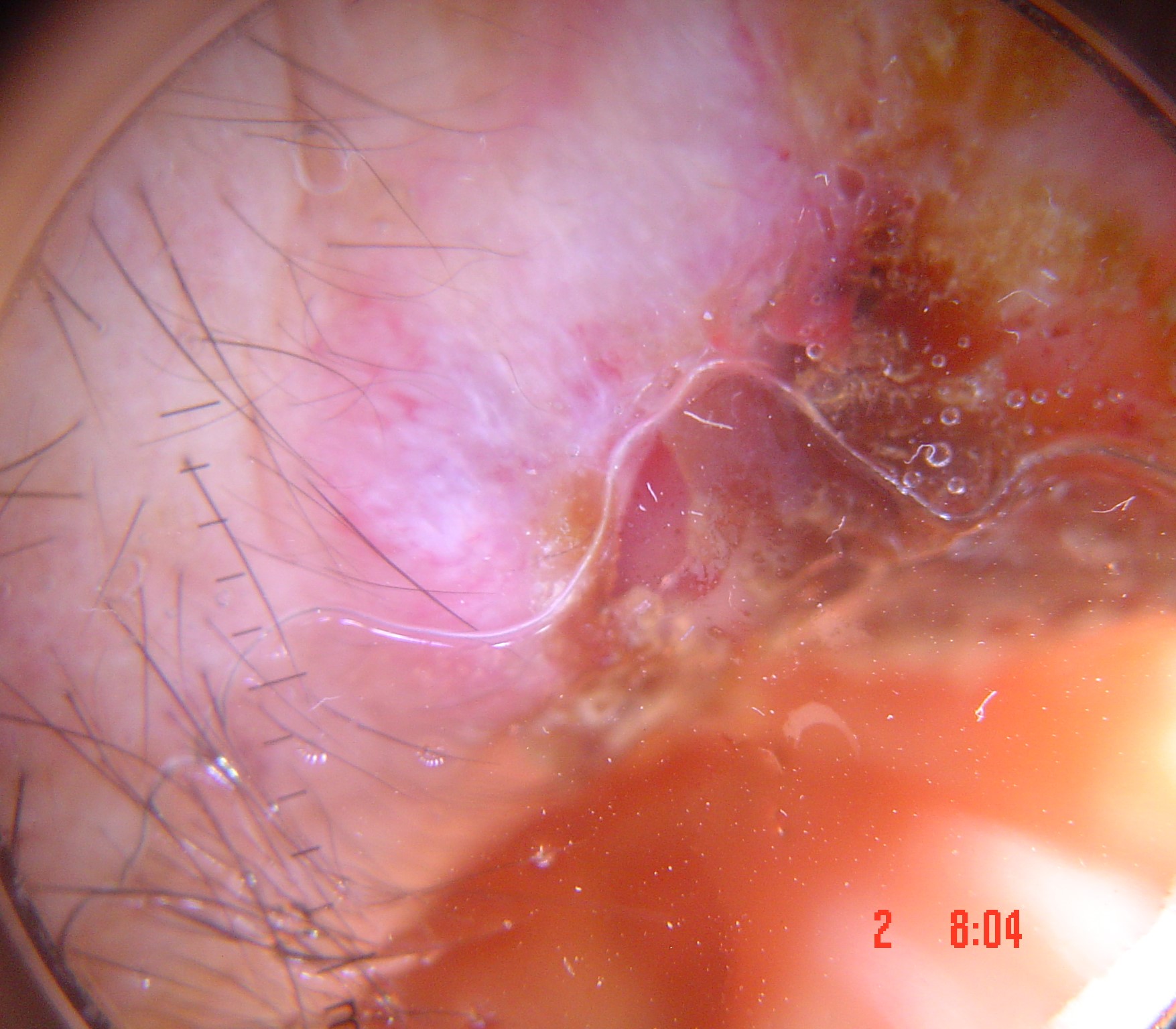image = dermatoscopy; label = squamous cell carcinoma (biopsy-proven).